The patient described the issue as a rash; the patient indicates burning and itching; the condition has been present for one to four weeks; the subject is 40–49, female; the lesion is described as raised or bumpy; no relevant systemic symptoms; the photograph was taken at an angle; the leg, arm and back of the torso are involved — 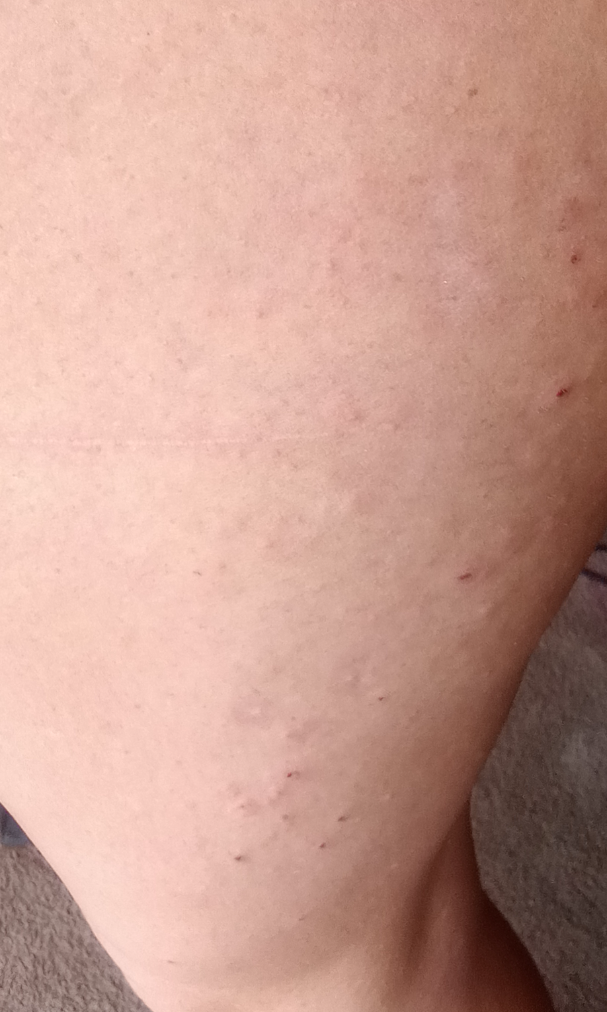Case summary:
- assessment · not assessable